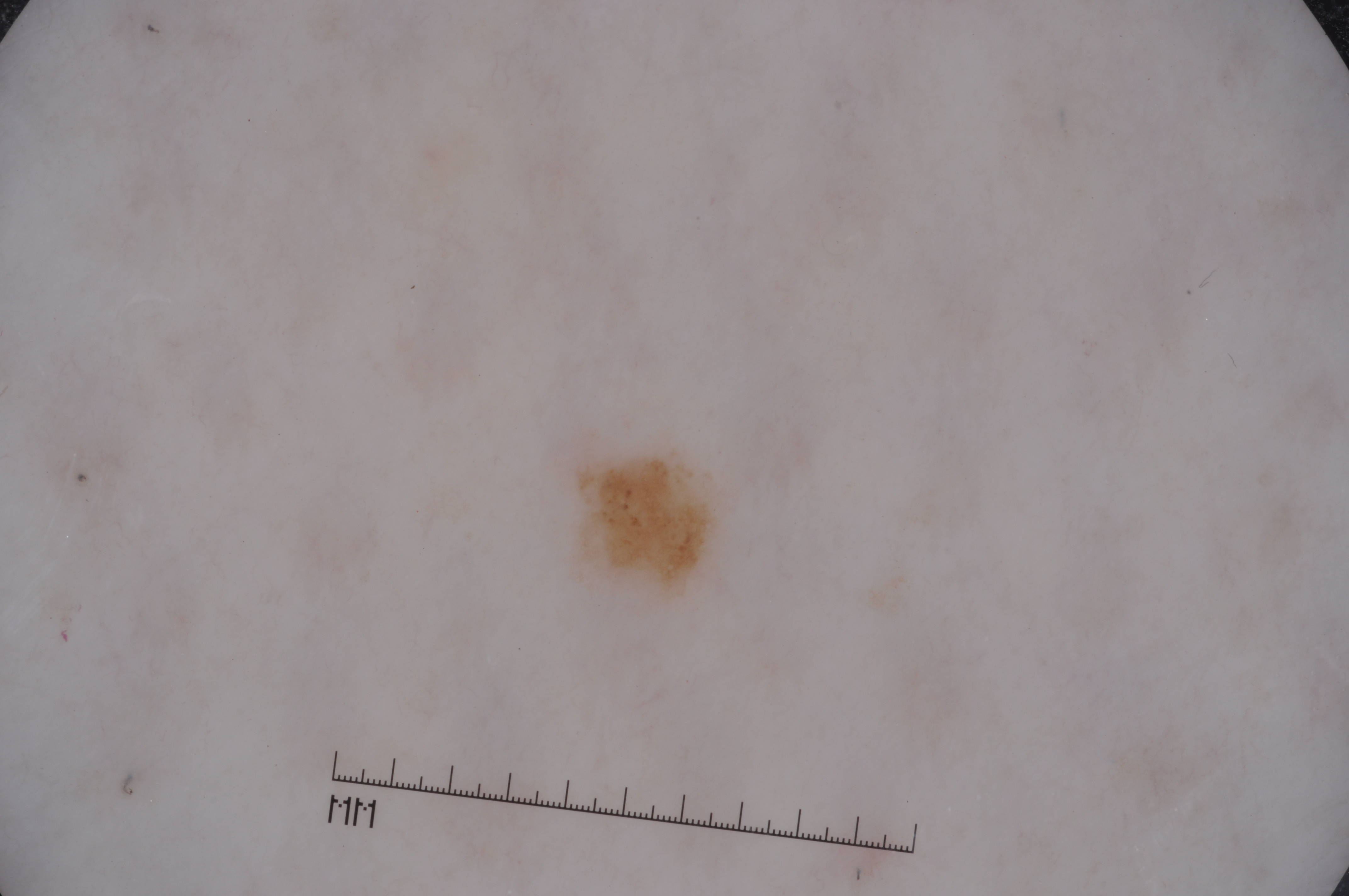Case summary:
* modality — dermoscopy
* subject — female, approximately 50 years of age
* lesion extent — ~1% of the field
* lesion location — 574 449 719 601
* features — pigment network
* impression — a melanocytic nevus, a benign lesion